A dermoscopic image of a skin lesion:
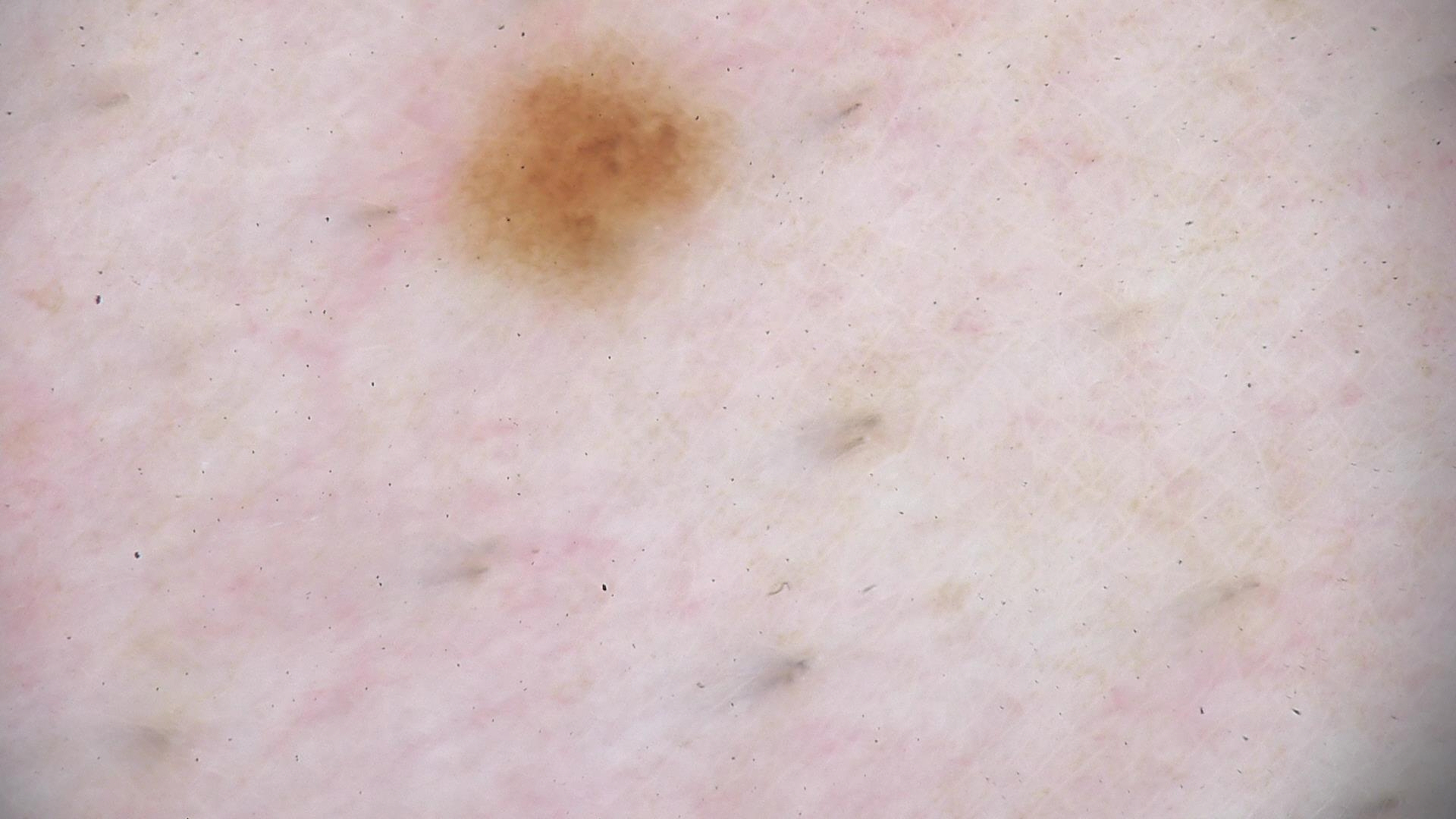label — dysplastic junctional nevus (expert consensus)